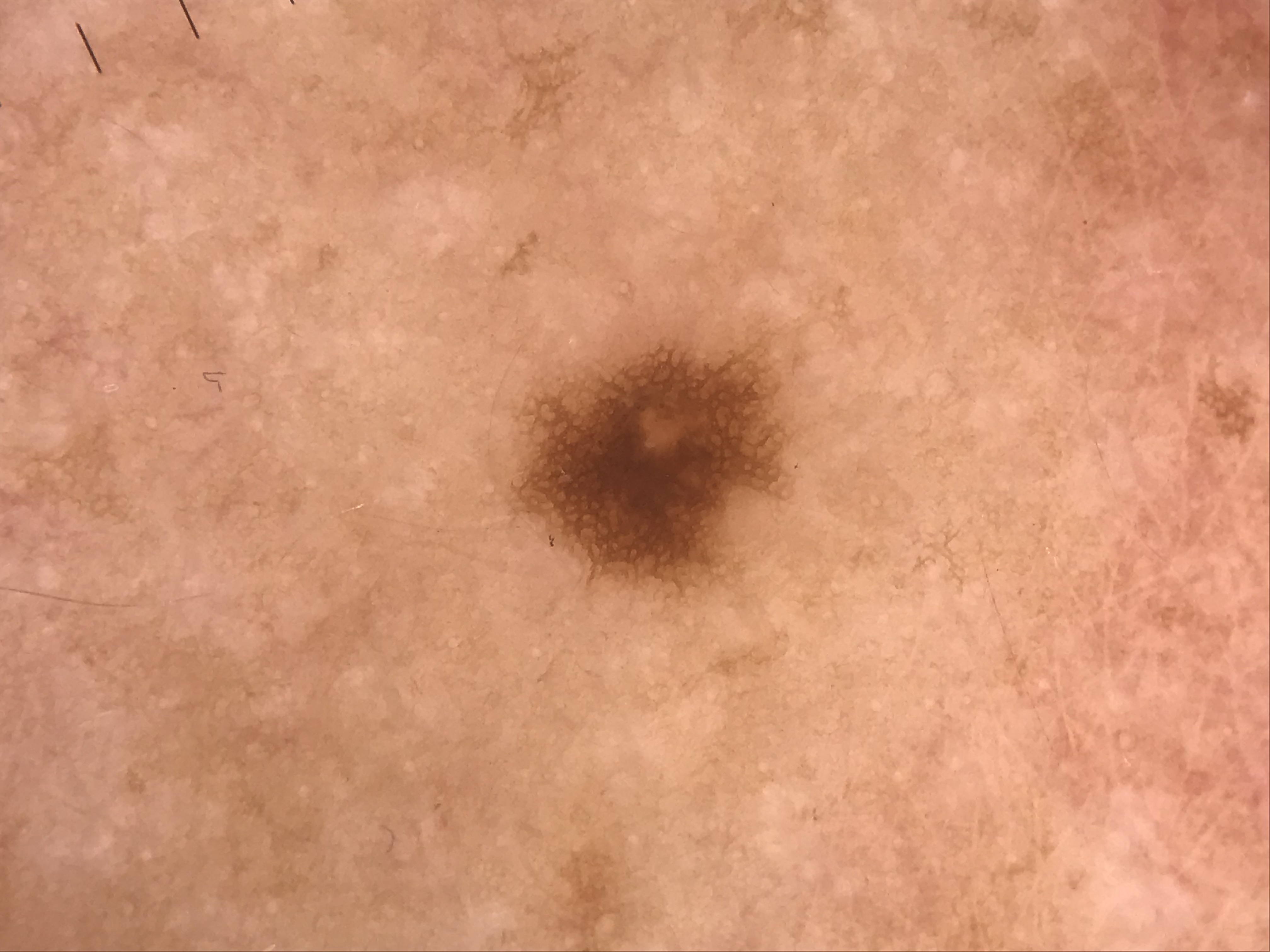Case:
* diagnostic label — junctional nevus (expert consensus)